The photograph is a close-up of the affected area. Located on the arm and leg. The subject is female.
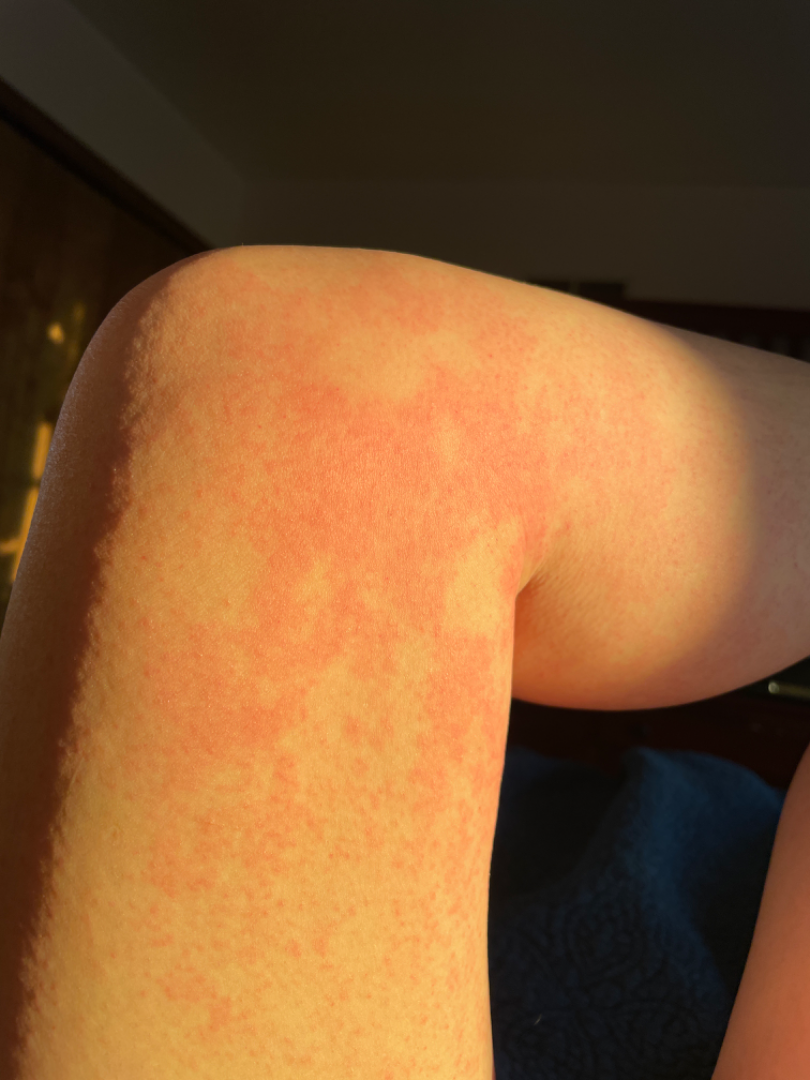dermatologist impression: most likely Eczema; with consideration of Drug Rash; an alternative is Urticaria.